A close-up photograph; the subject is 18–29, male; located on the head or neck: 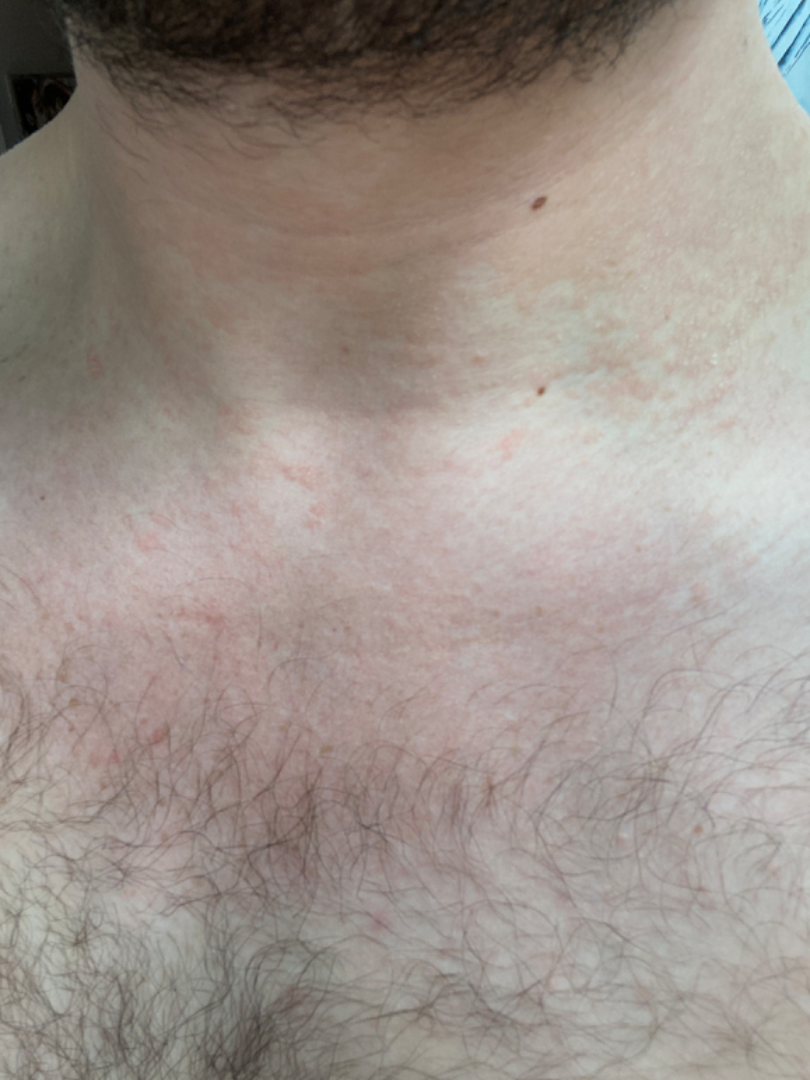Q: What was the assessment?
A: could not be assessed